The affected area is the back of the hand, the photograph is a close-up of the affected area — 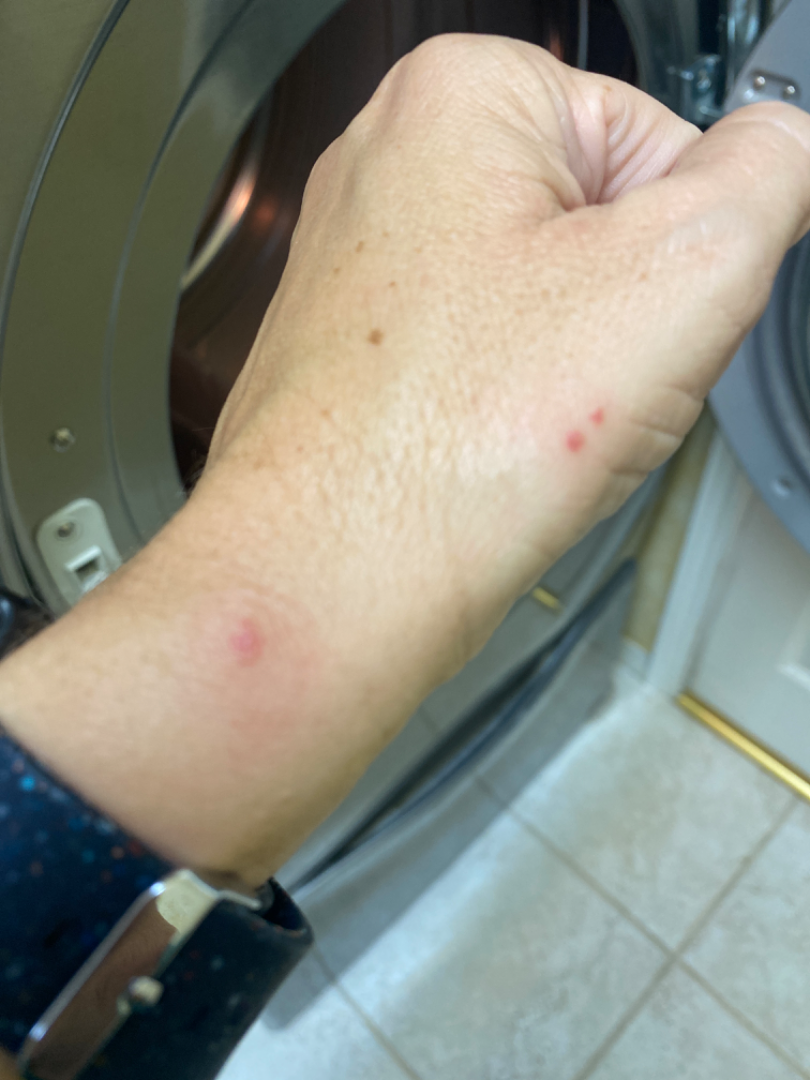On photographic review, Insect Bite (leading); Eczema (possible); Allergic Contact Dermatitis (possible).